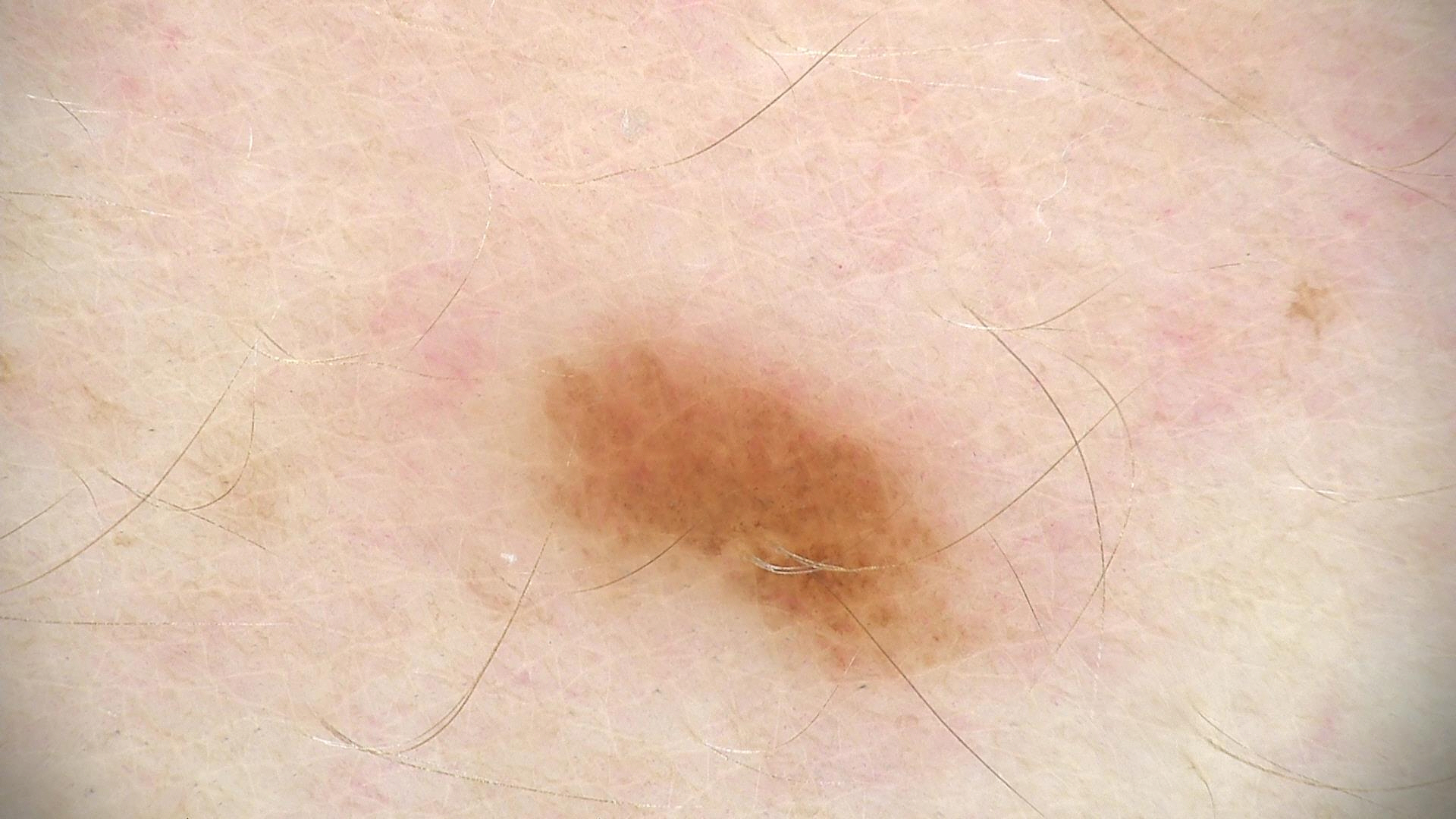Findings: A skin lesion imaged with a dermatoscope. Impression: Diagnosed as a benign lesion — a dysplastic junctional nevus.